The contributor notes the condition has been present for less than one week. Texture is reported as flat. The leg is involved. The patient reported no relevant symptoms from the lesion. The photo was captured at an angle. Fitzpatrick I; lay graders estimated MST 2 — 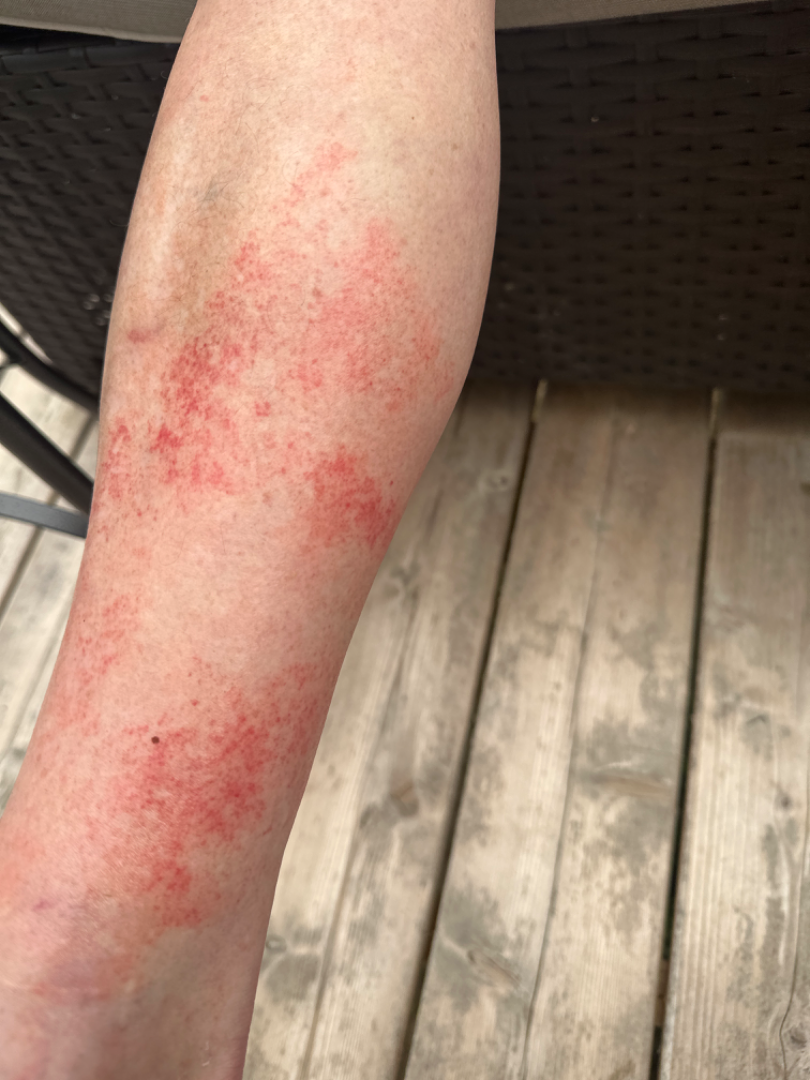Notes:
– clinical impression — a single dermatologist reviewed the case: the favored diagnosis is Pigmented purpuric eruption; also on the differential is Leukocytoclastic Vasculitis; less likely is Allergic Contact Dermatitis